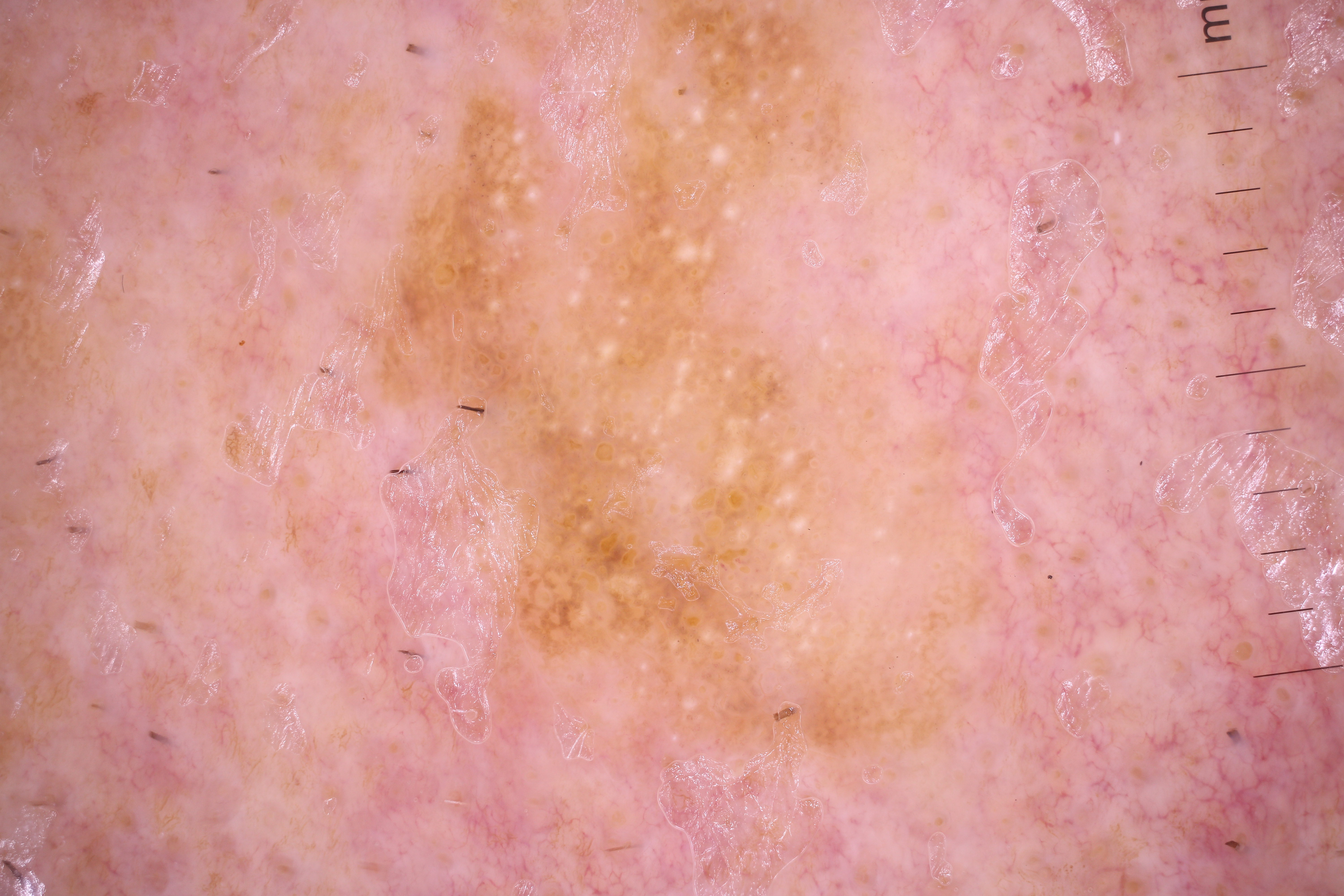A skin lesion imaged with a dermatoscope.
As (left, top, right, bottom), the lesion is located at [339,2,1026,788].
Expert review diagnosed this as a seborrheic keratosis.